Female contributor, age 30–39 · this image was taken at an angle:
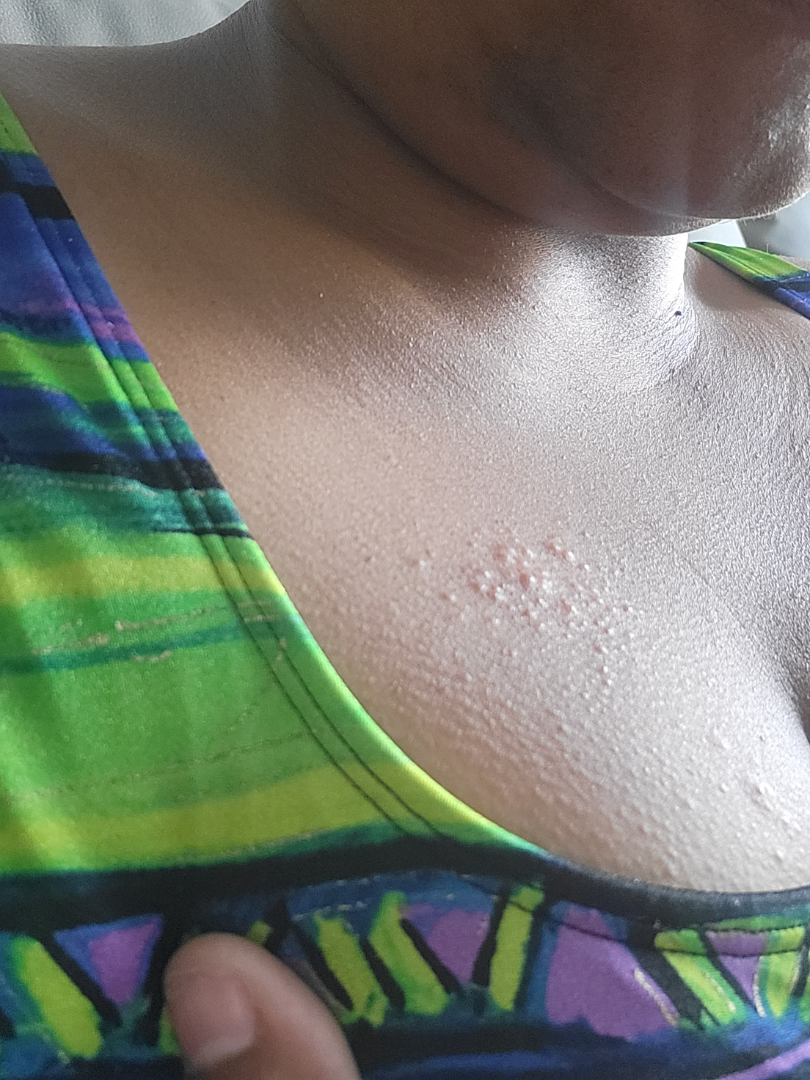The reviewing dermatologist's impression was: Insect Bite, Herpes Zoster and Allergic Contact Dermatitis were considered with similar weight.